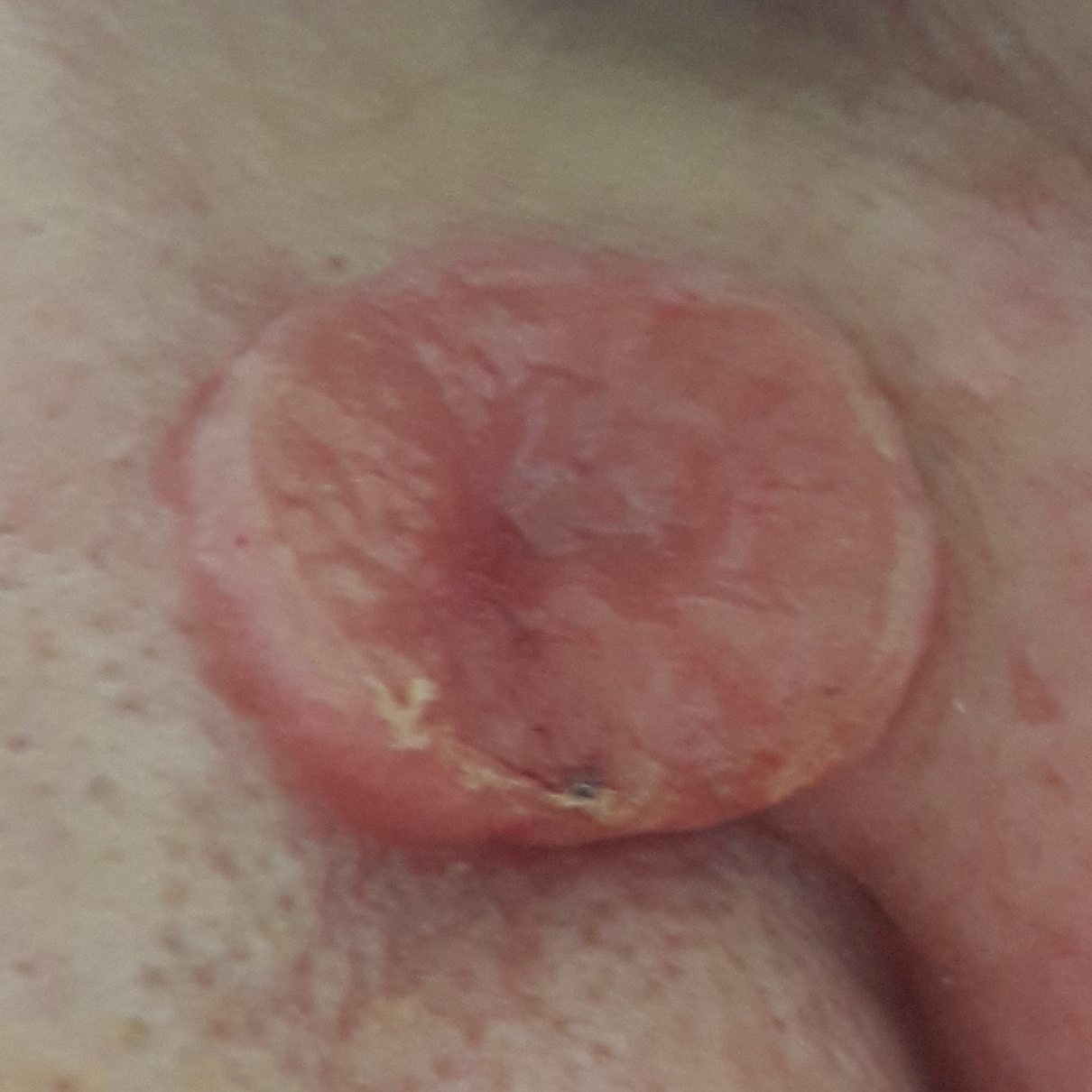A clinical photograph showing a skin lesion.
A female patient 58 years of age.
The chart notes prior malignancy (patient or family) and prior skin cancer (patient or family).
The patient was assessed as Fitzpatrick phototype III.
The lesion is on the nose.
The lesion measures approximately 17 × 14 mm.
Per patient report, the lesion has changed, hurts, has grown, has bled, is elevated, and itches.
On biopsy, the diagnosis was a basal cell carcinoma.